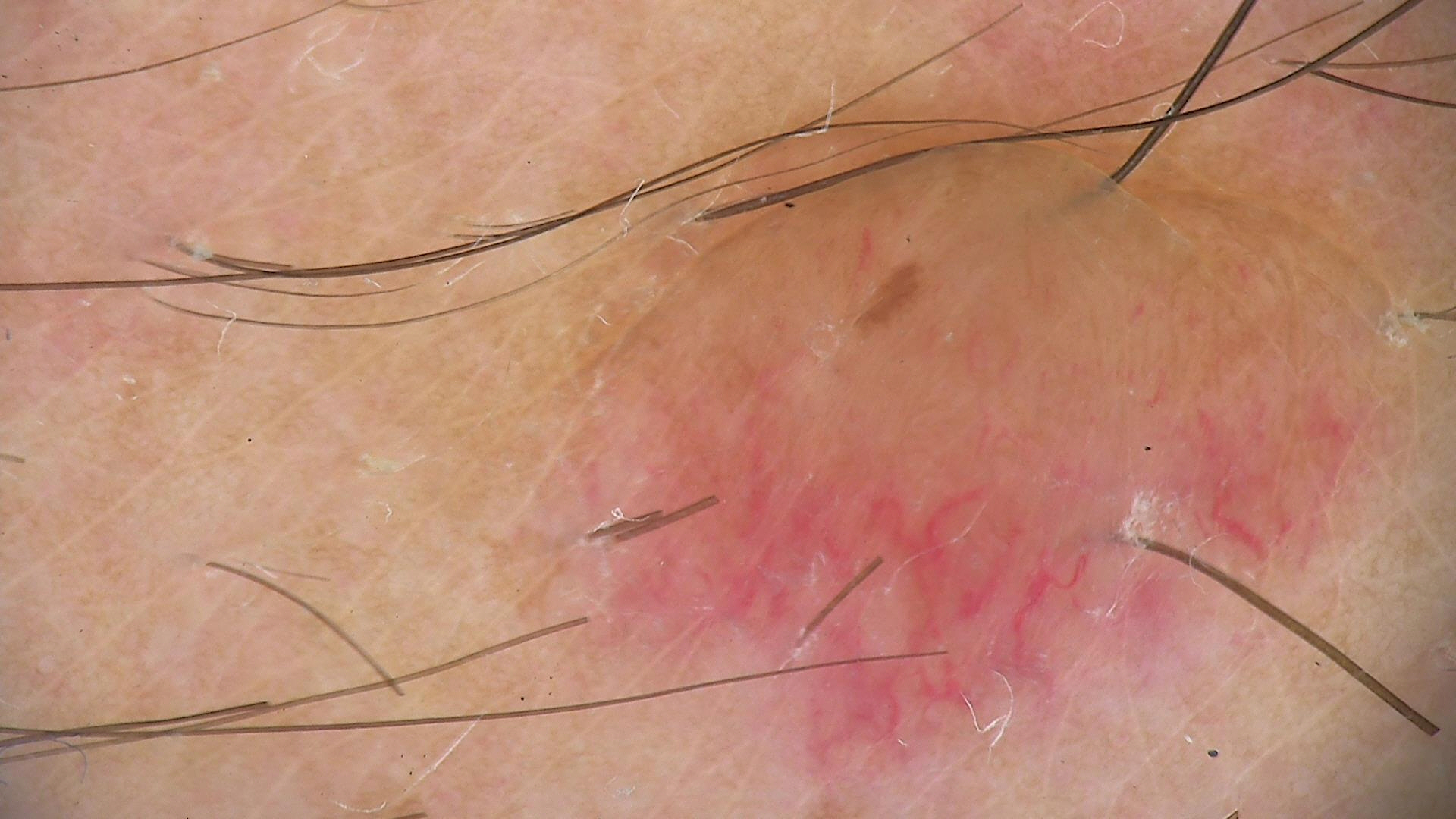subtype — banal | class — dermal nevus (expert consensus).